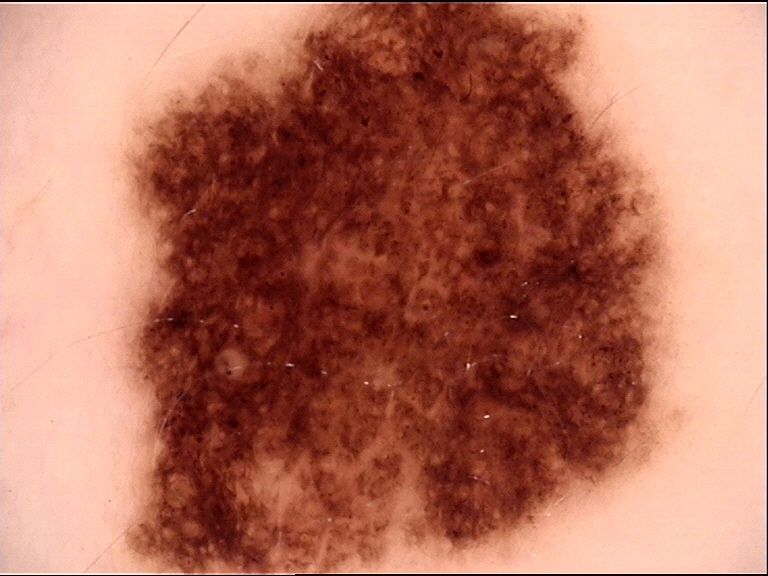- assessment — dysplastic compound nevus (expert consensus)